Located on the arm, front of the torso, back of the torso and leg. Male contributor, age 40–49. A close-up photograph — 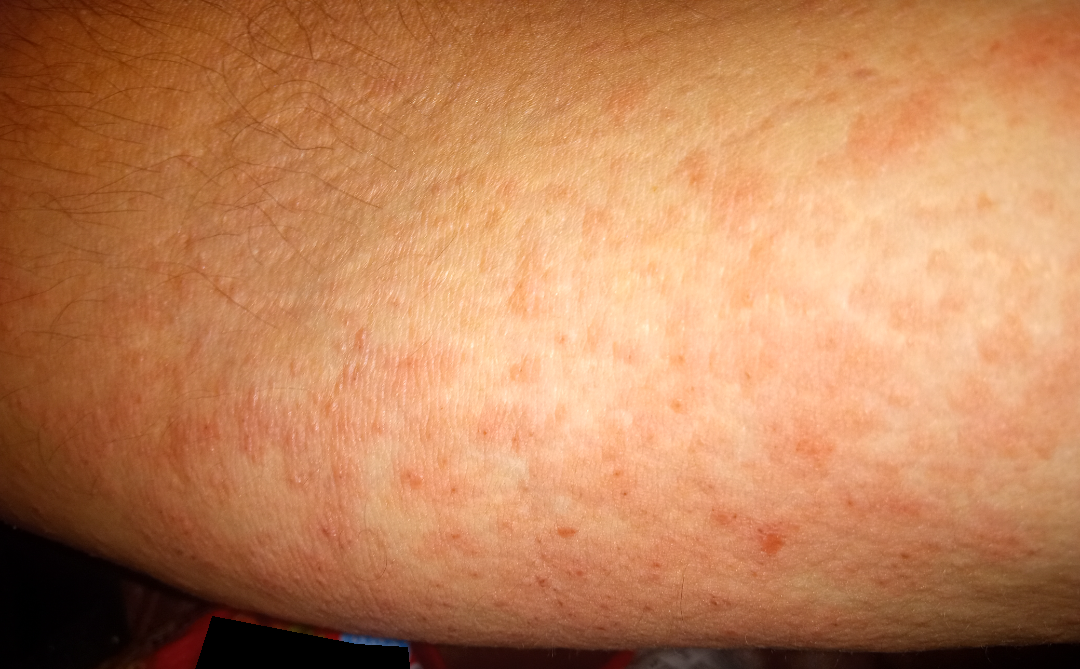The dermatologist could not determine a likely condition from the photograph alone.